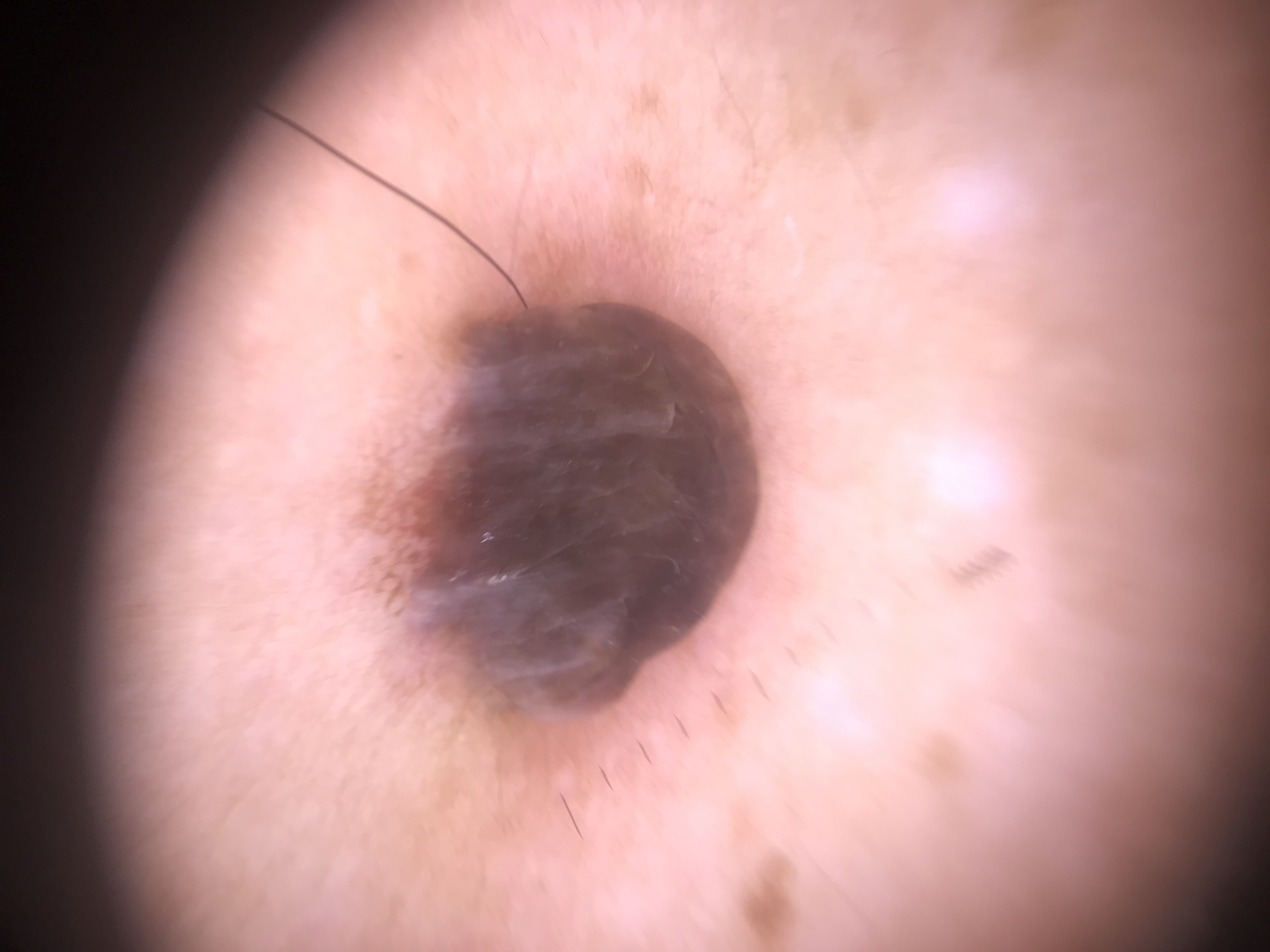Case: A dermoscopic photograph of a skin lesion. Impression: Diagnosed as a dermal nevus.